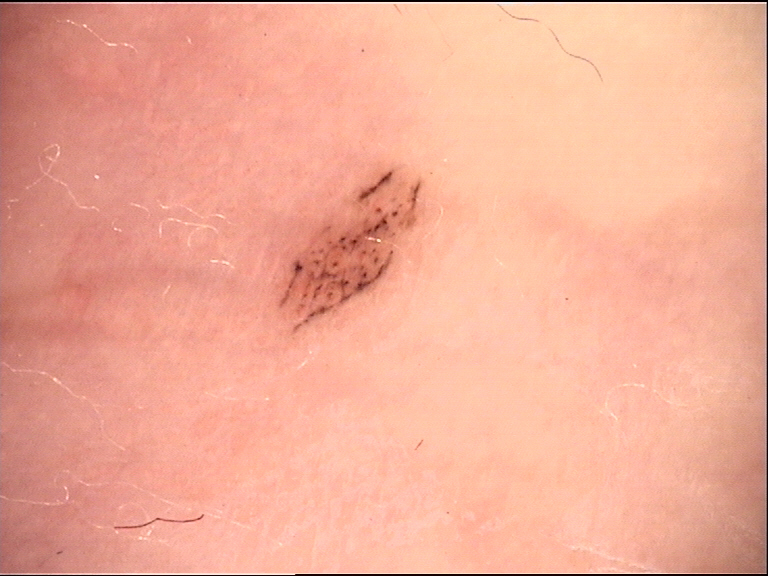Summary: A dermoscopy image of a single skin lesion. Conclusion: The diagnostic label was a benign lesion — an acral dysplastic junctional nevus.